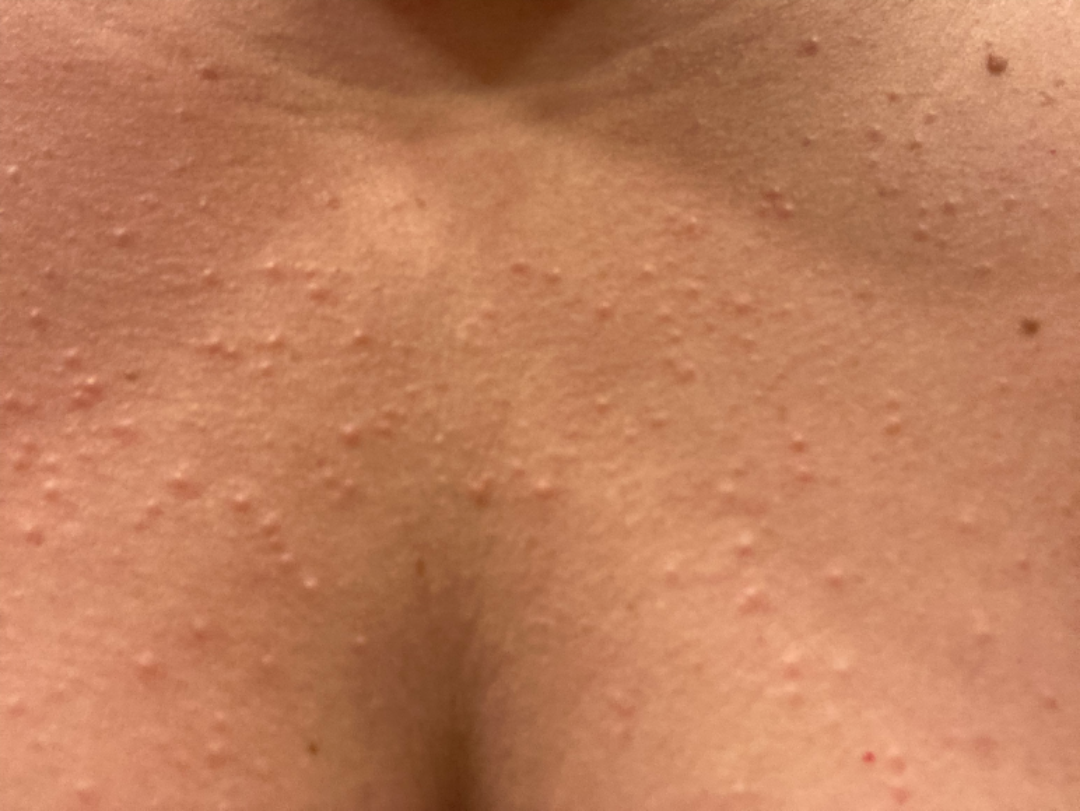shot type=close-up | subject=female, age 40–49 | affected area=head or neck | impression=single-reviewer assessment: in keeping with Folliculitis.